The patient reports the lesion is fluid-filled and raised or bumpy; the patient reports bleeding, pain and itching; skin tone: human graders estimated MST 1 or 2; reported duration is one to four weeks; located on the arm and leg; this image was taken at a distance:
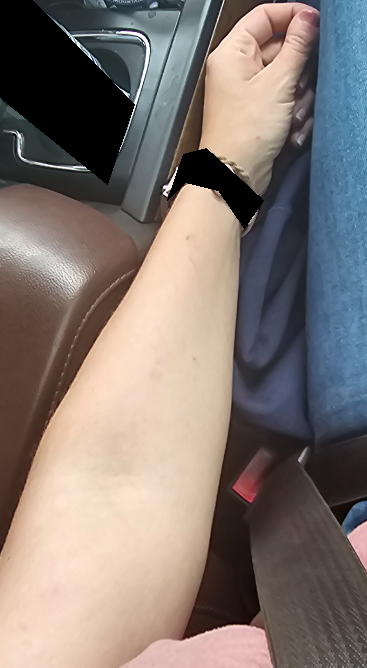Notes:
* assessment · not assessable